A subject aged 82.
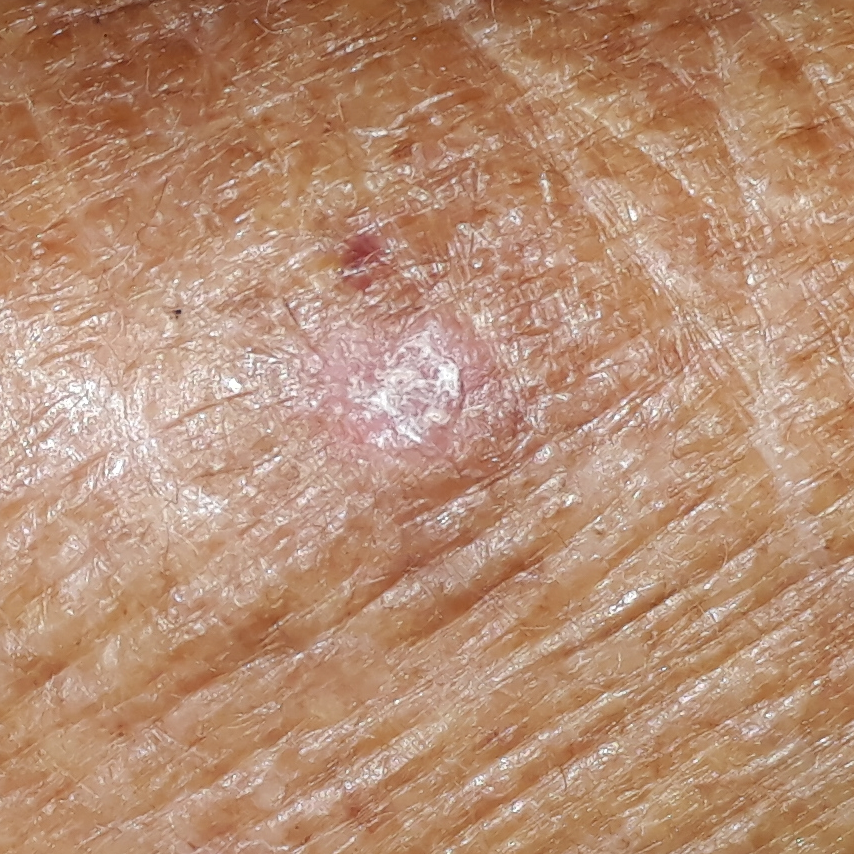The lesion was found on a forearm. Per patient report, the lesion is elevated, but does not itch and does not hurt. Clinically diagnosed as an actinic keratosis.